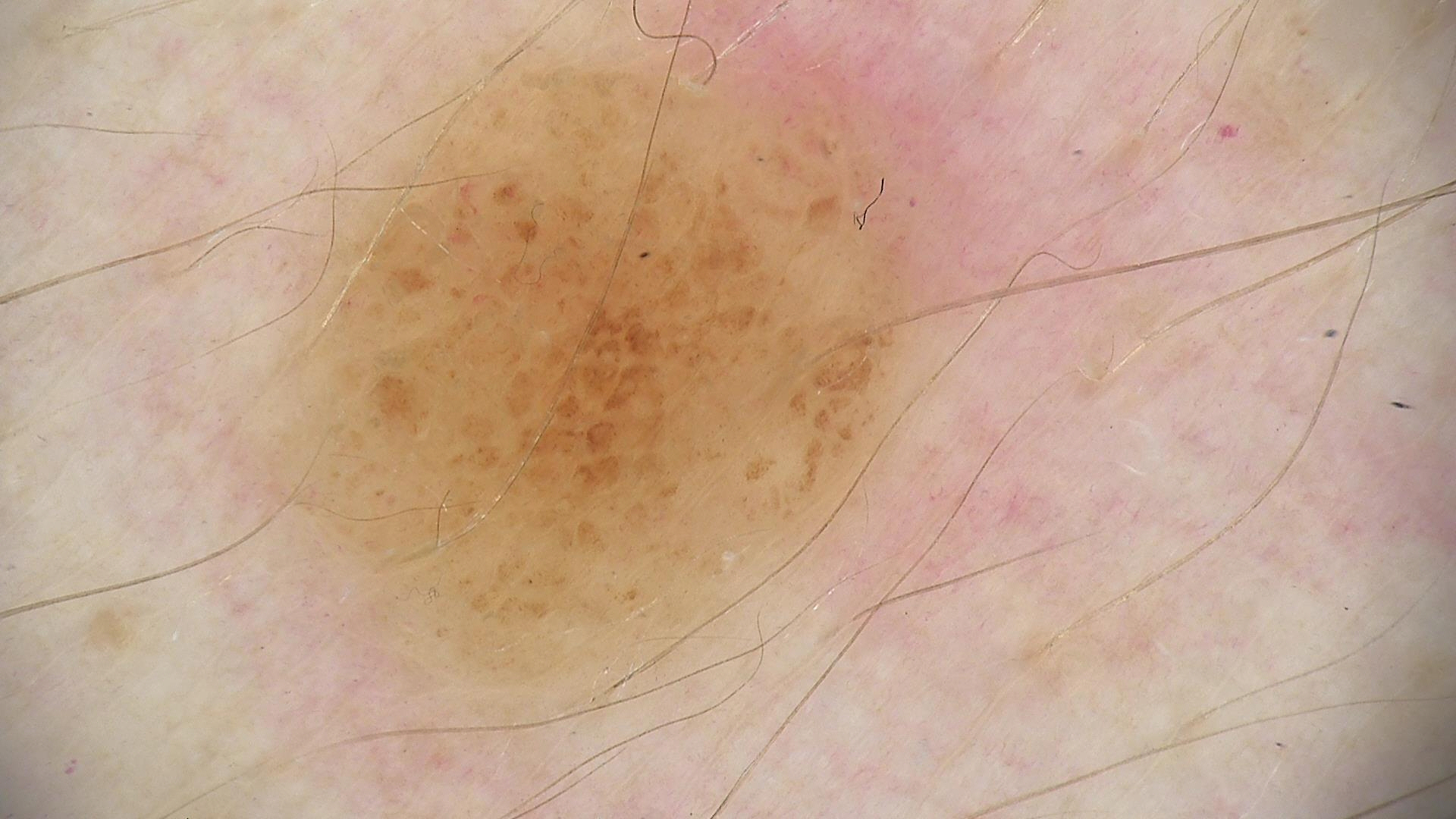  lesion_type:
    main_class: banal
    pattern: compound
  diagnosis:
    name: compound nevus
    code: cb
    malignancy: benign
    super_class: melanocytic
    confirmation: expert consensus